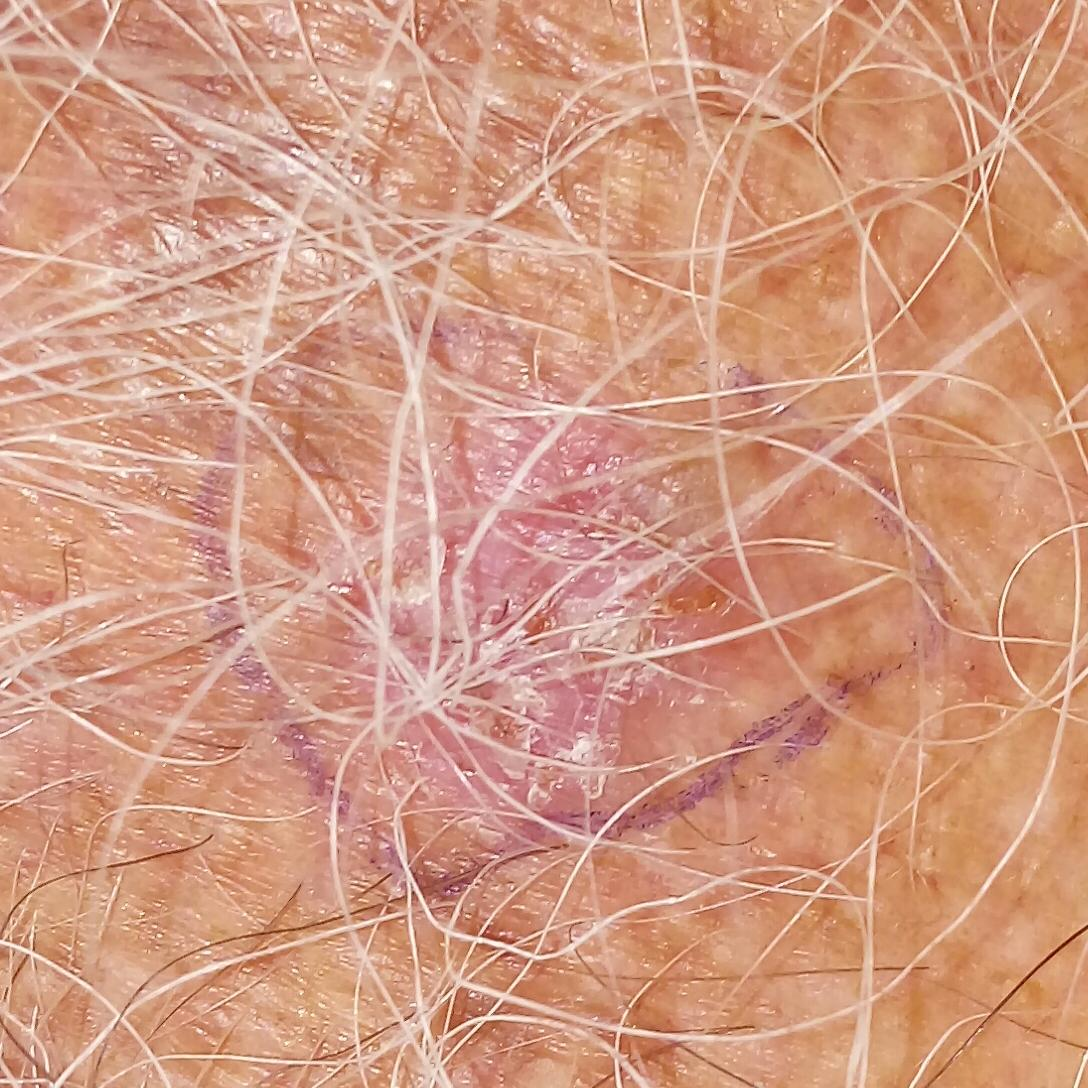The biopsy diagnosis was a basal cell carcinoma.